The patient describes having few moles overall · a male patient aged 66 · referred with a clinical suspicion of basal cell carcinoma · a macroscopic clinical photograph of a skin lesion · on a questionnaire the patient reported a prior organ transplant.
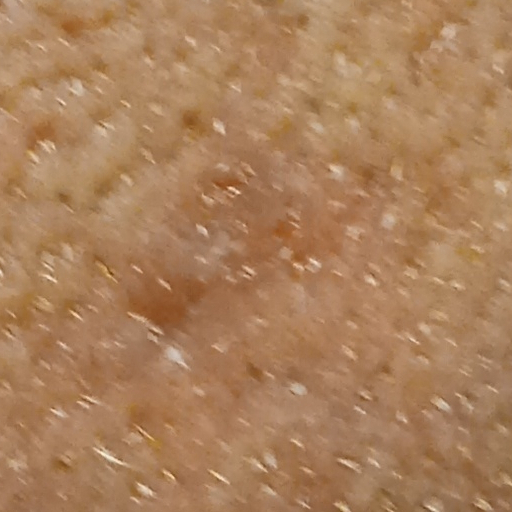Findings: Located on the face. The lesion is about 7.5 mm across. Diagnosis: Histopathology confirmed a basal cell carcinoma, following excision, with a measured tumor thickness of 1.9 mm.